A skin lesion imaged with a dermatoscope. A female subject roughly 45 years of age — 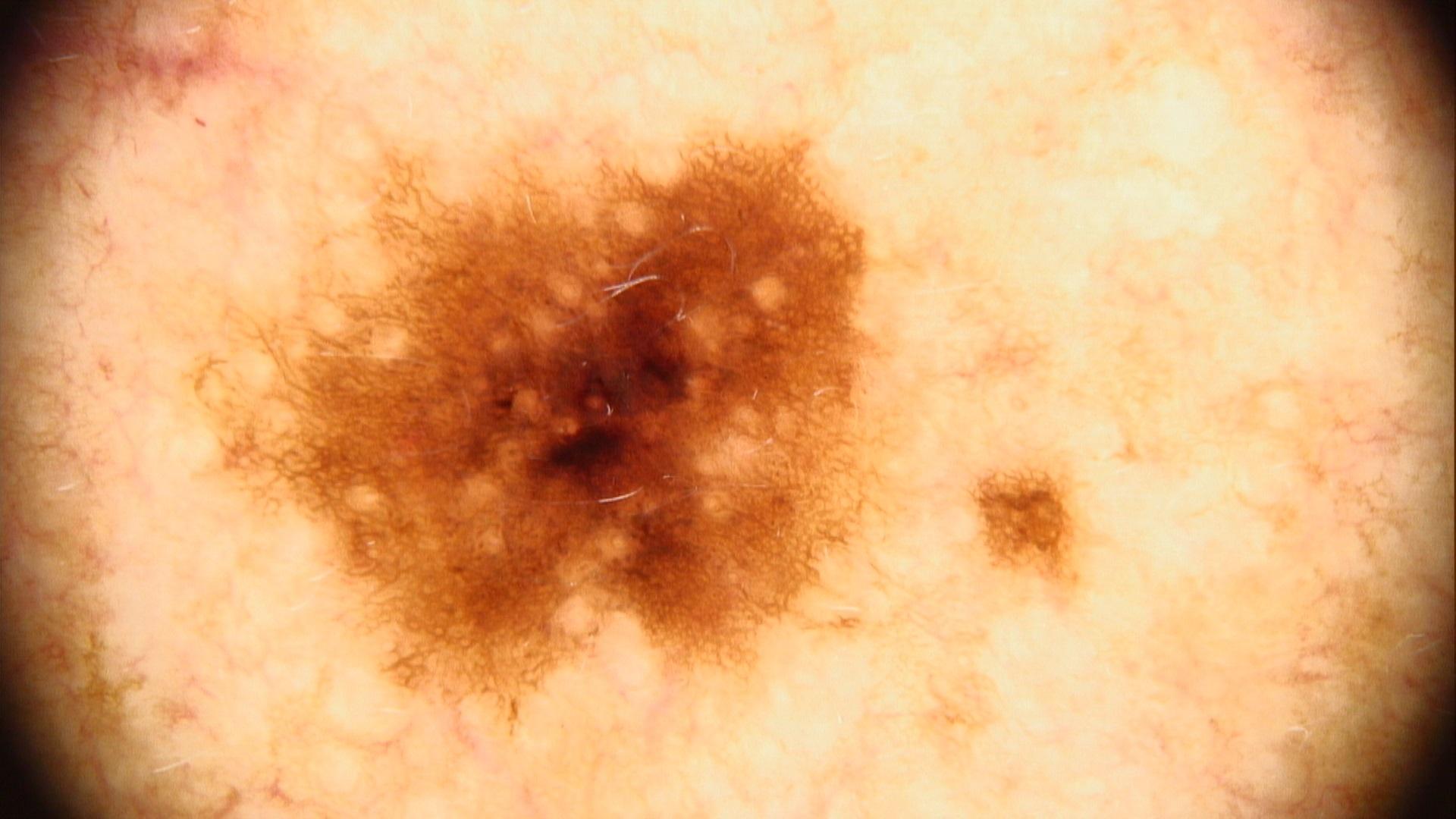Pathology: On biopsy, the diagnosis was a benign lesion — a nevus.